A dermatoscopic image of a skin lesion.
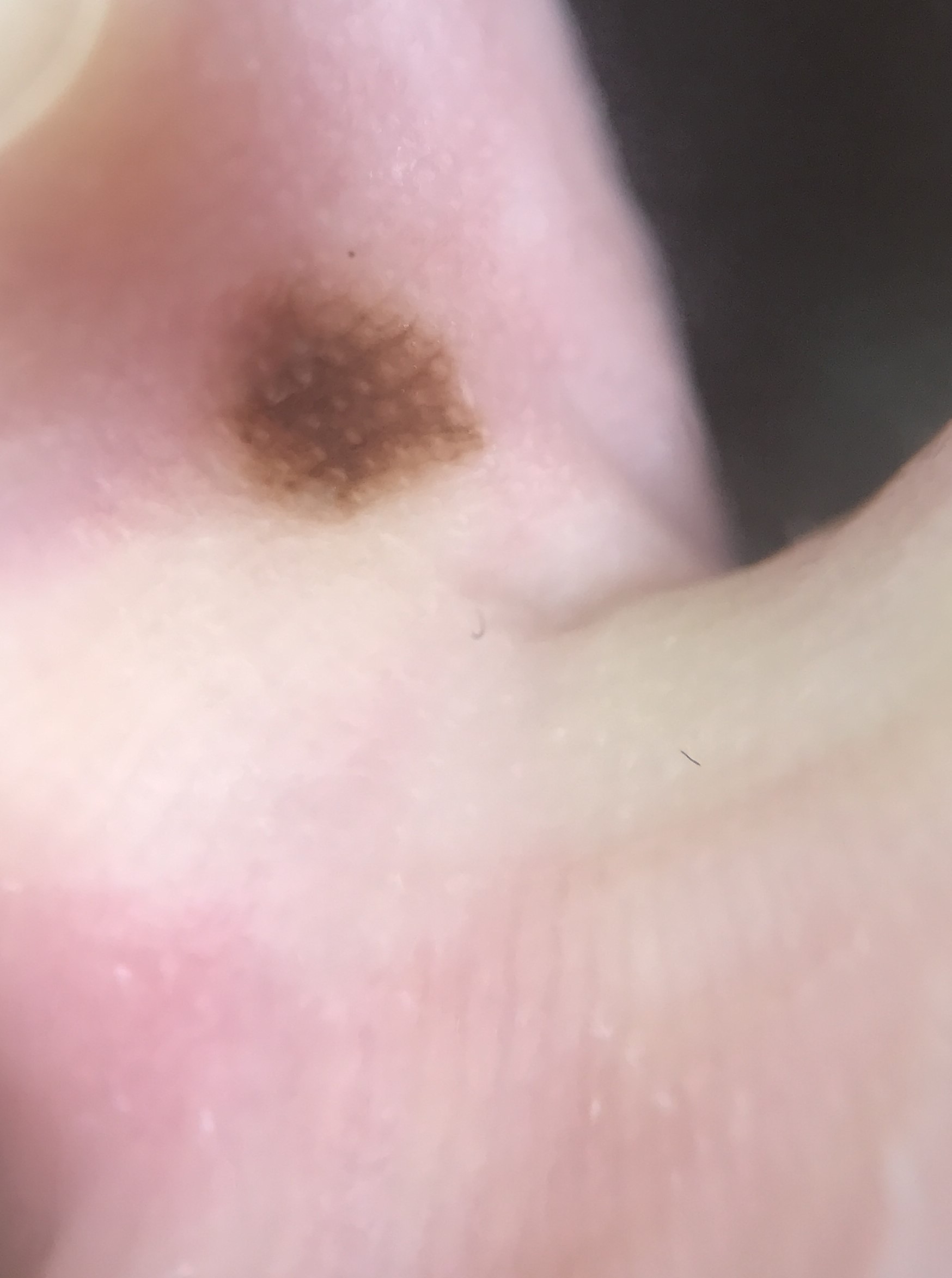This is a banal lesion.
Classified as an acral junctional nevus.